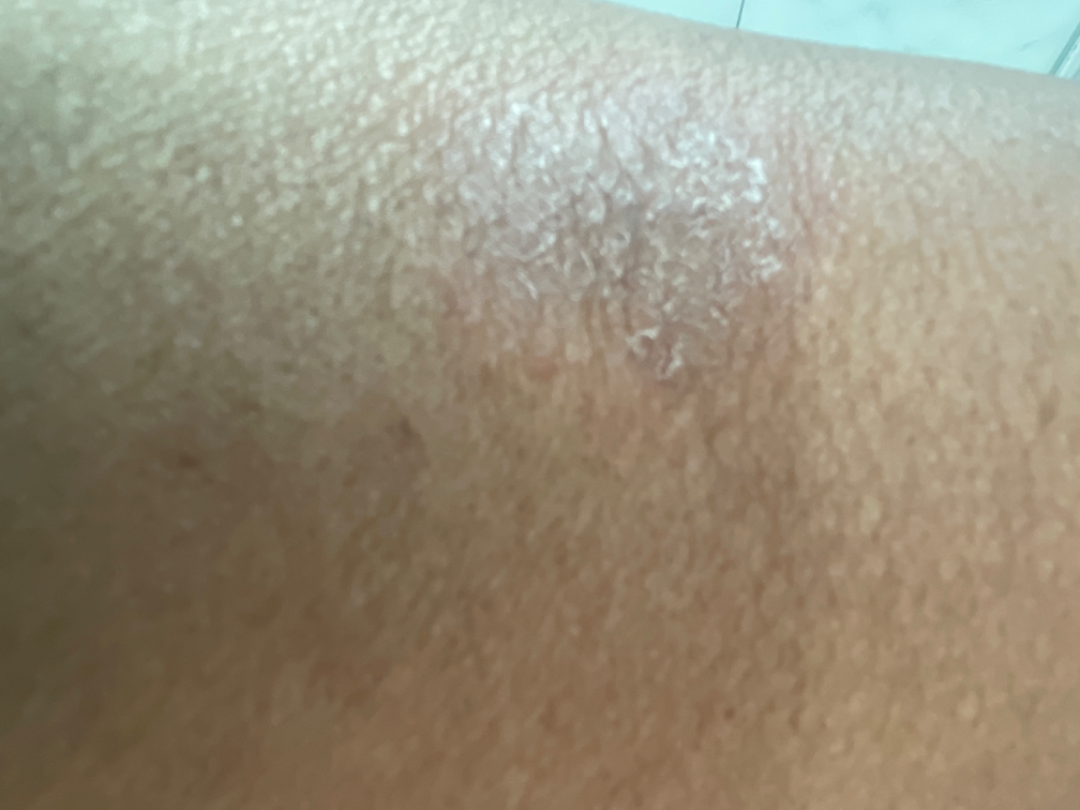The lesion is described as rough or flaky. The patient notes the condition has been present for one to four weeks. The photograph was taken at an angle. Skin tone: Fitzpatrick IV; human graders estimated Monk skin tone scale 7 (US pool) or 3 (India pool). The lesion involves the leg. The patient notes enlargement. Eczema (33%); Impetigo (33%); Psoriasis (33%).